A skin lesion imaged with a dermatoscope: 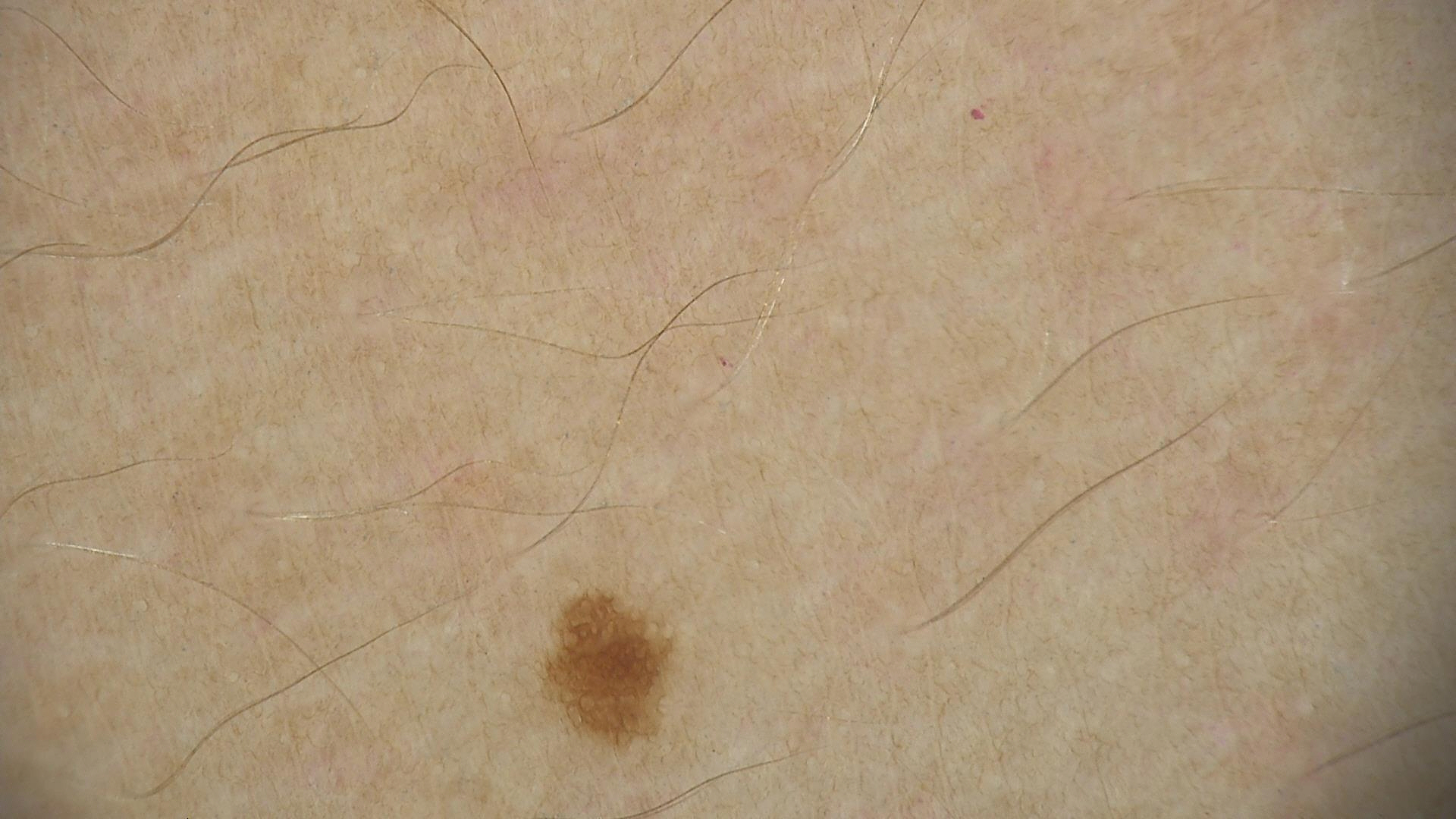The morphology is that of a banal lesion.
Consistent with a junctional nevus.